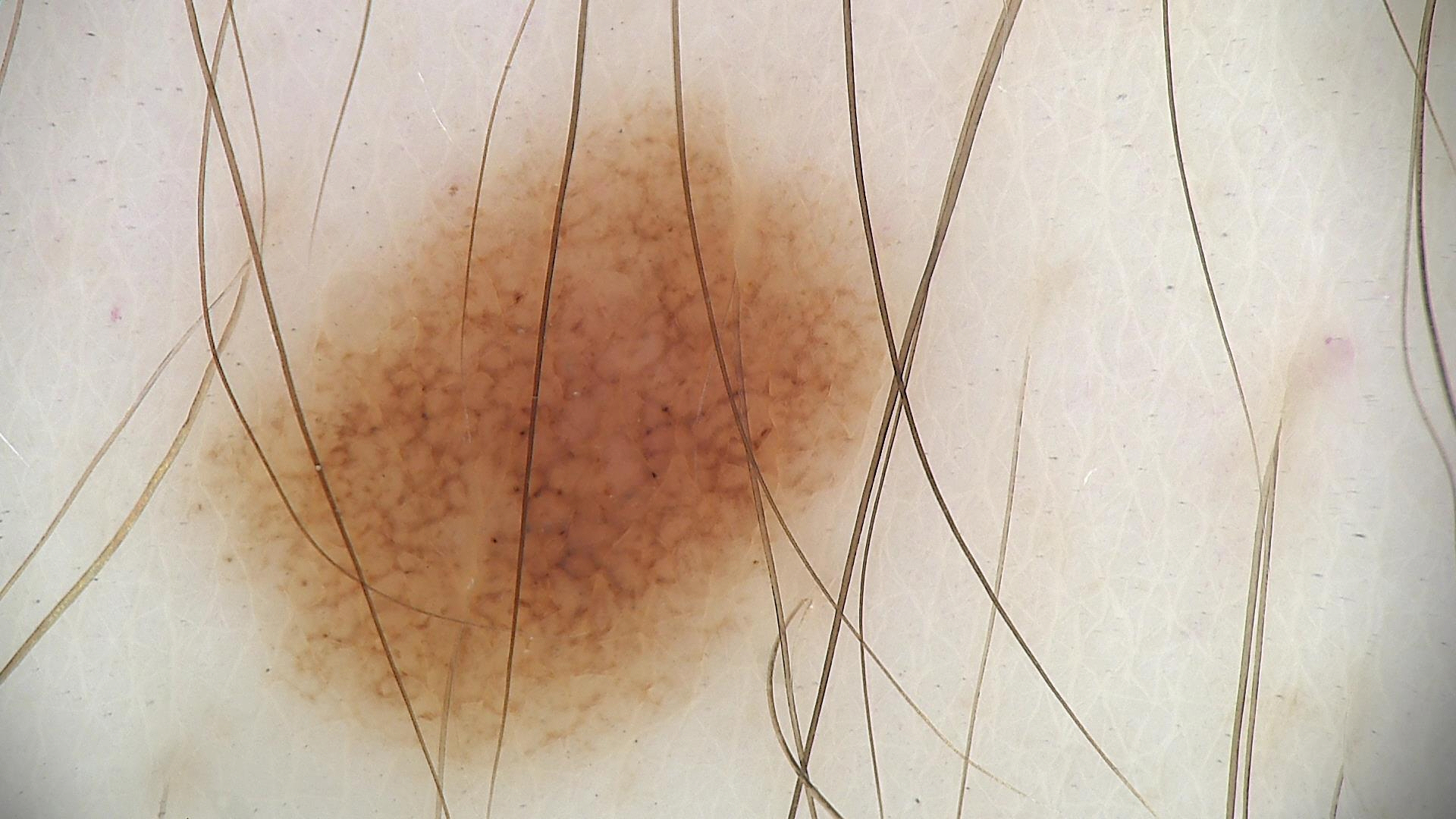modality — dermatoscopy
class — dysplastic junctional nevus (expert consensus)